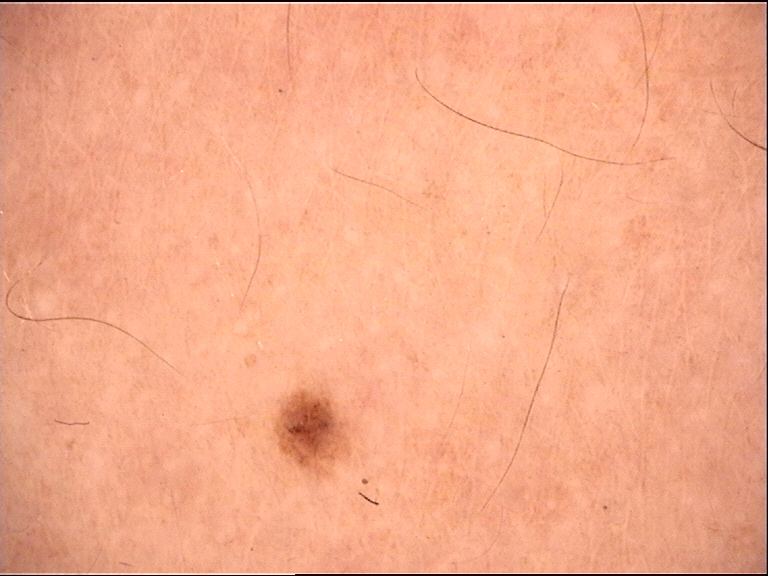| field | value |
|---|---|
| class | dysplastic junctional nevus (expert consensus) |